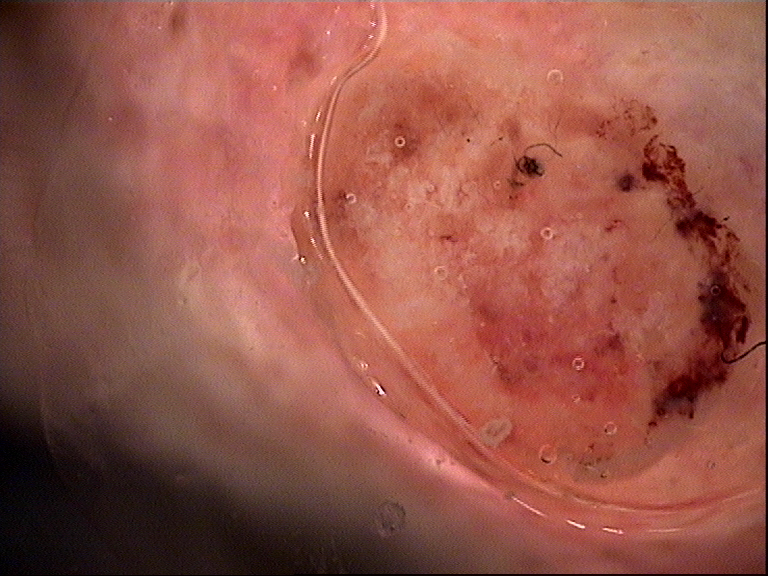A dermoscopy image of a single skin lesion. Biopsy-confirmed as a malignant, keratinocytic lesion — a squamous cell carcinoma.